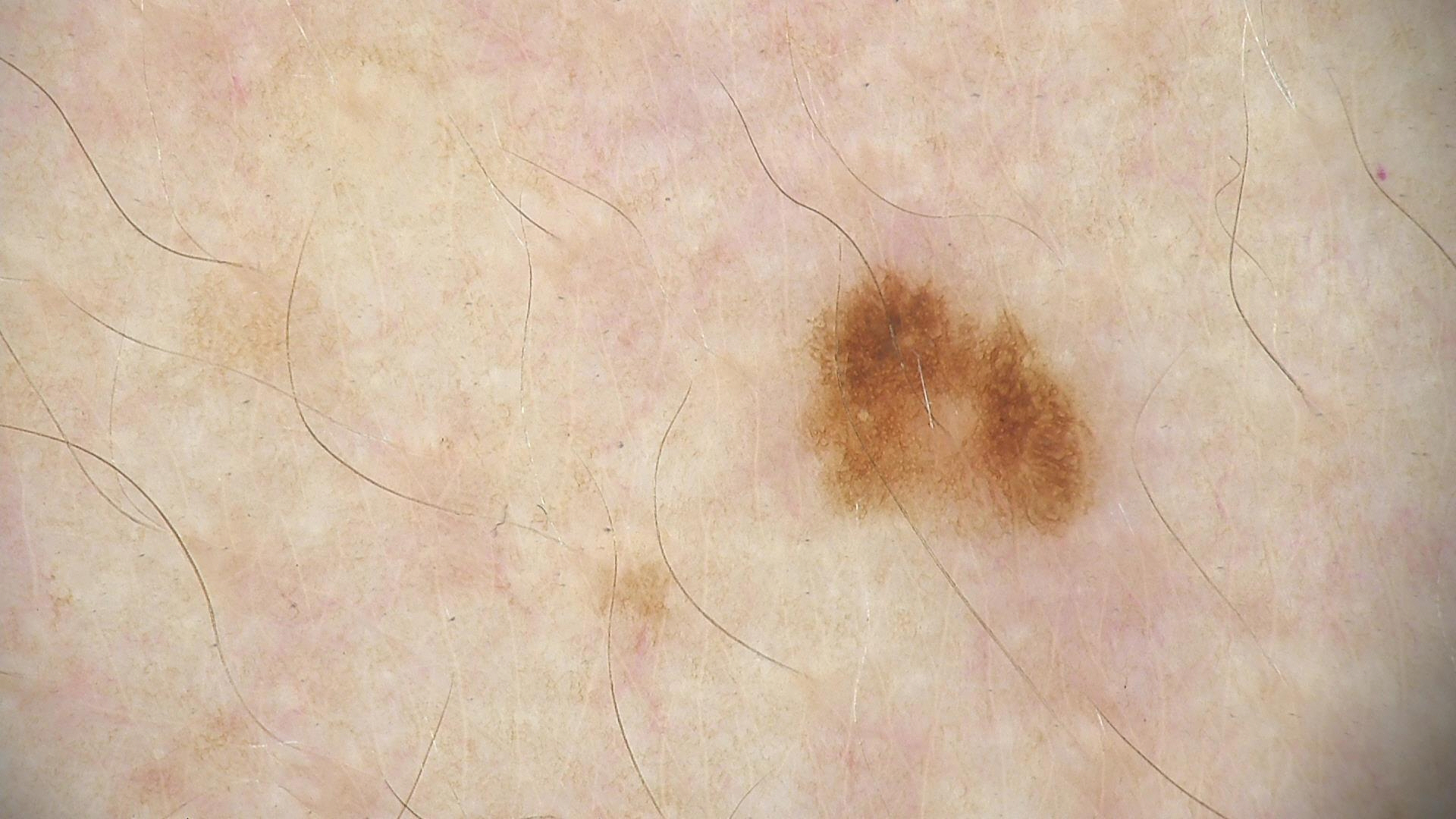Labeled as a dysplastic junctional nevus.